A dermoscopic image of a skin lesion:
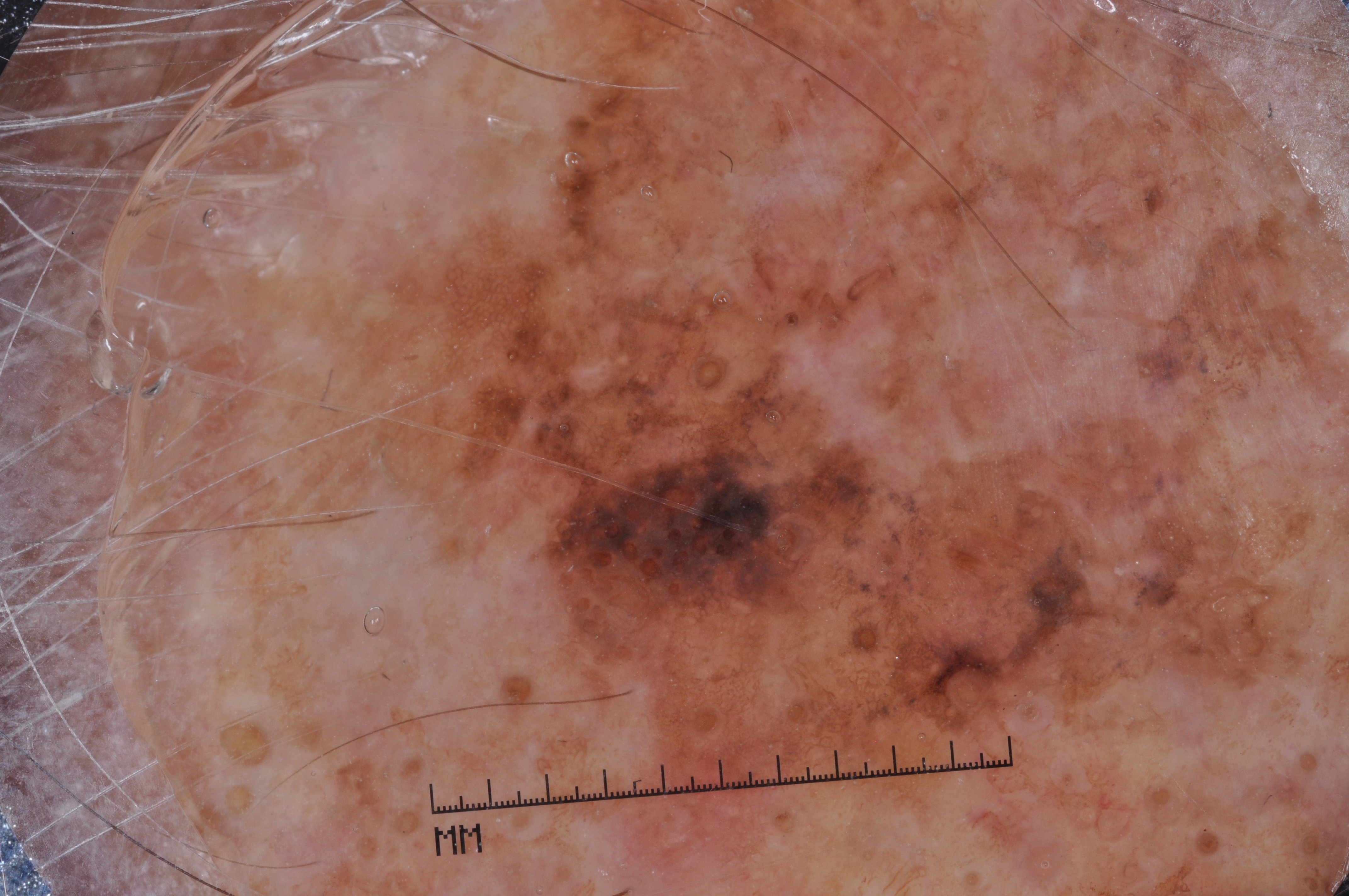Summary: In (x1, y1, x2, y2) order, the lesion occupies the region [150, 0, 1344, 893]. On dermoscopy, the lesion shows pigment network and milia-like cysts, with no negative network or streaks. Pathology: On biopsy, the diagnosis was a melanoma.